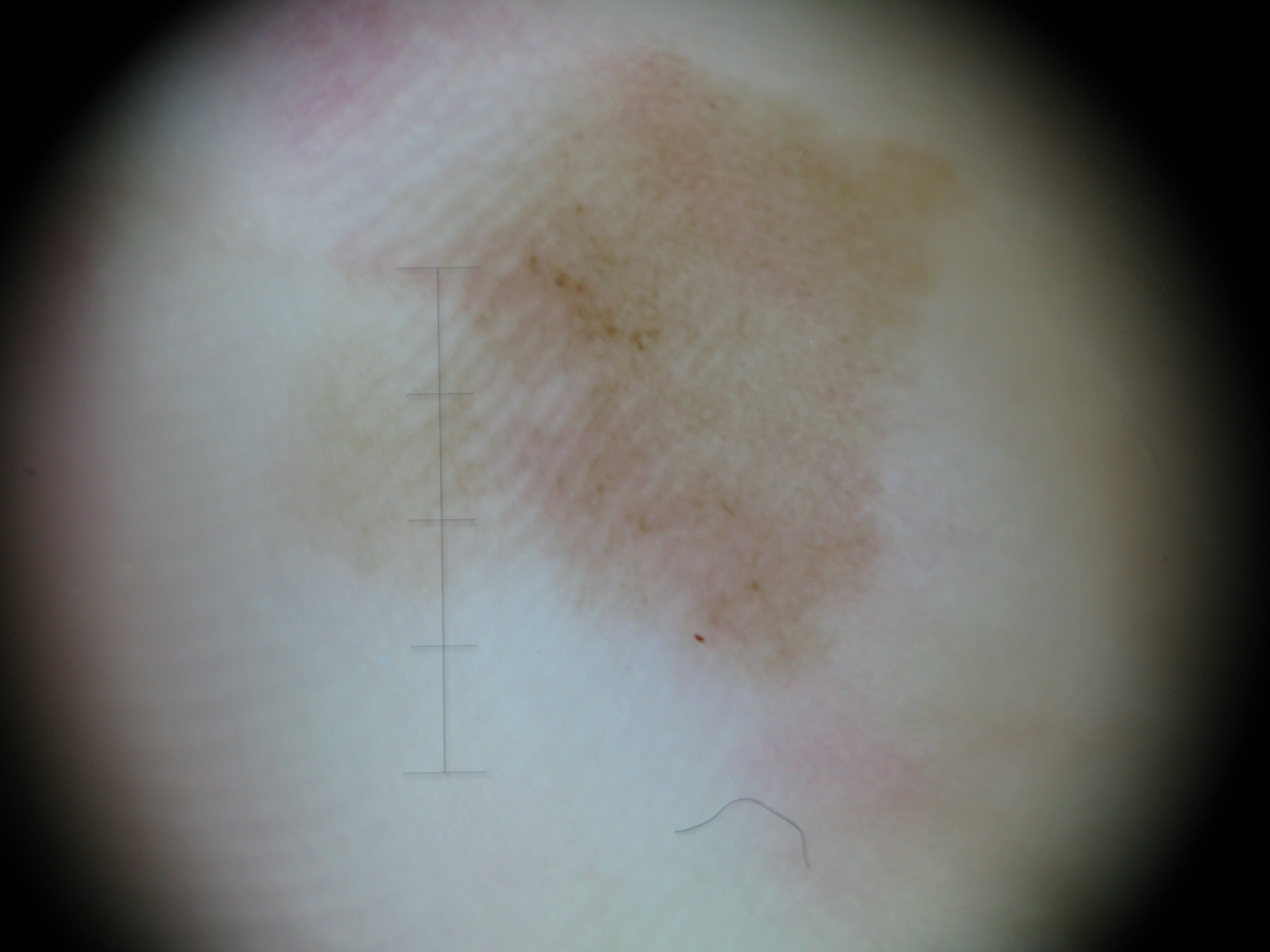class = acral junctional nevus (expert consensus).